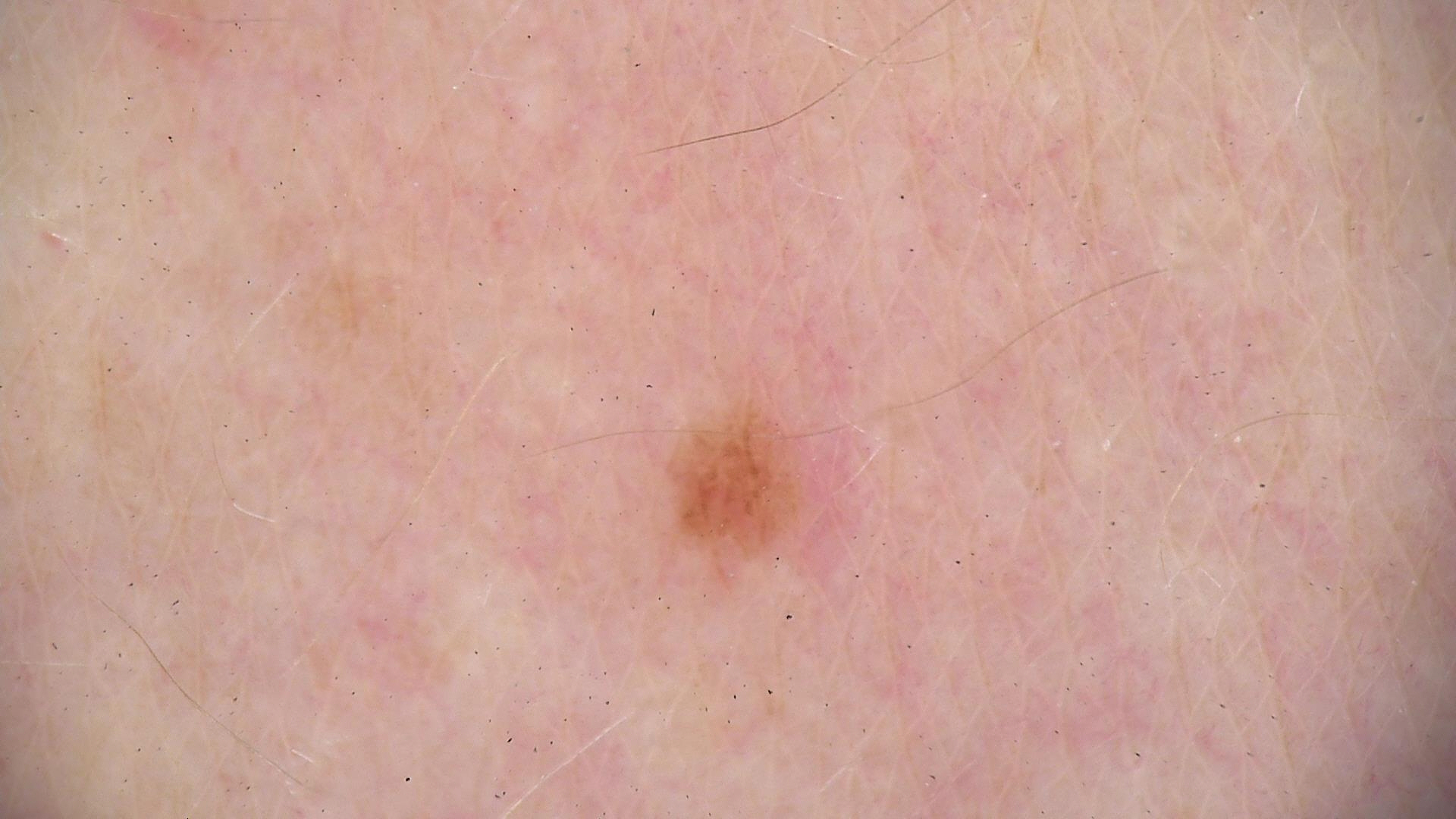– label — junctional nevus (expert consensus)